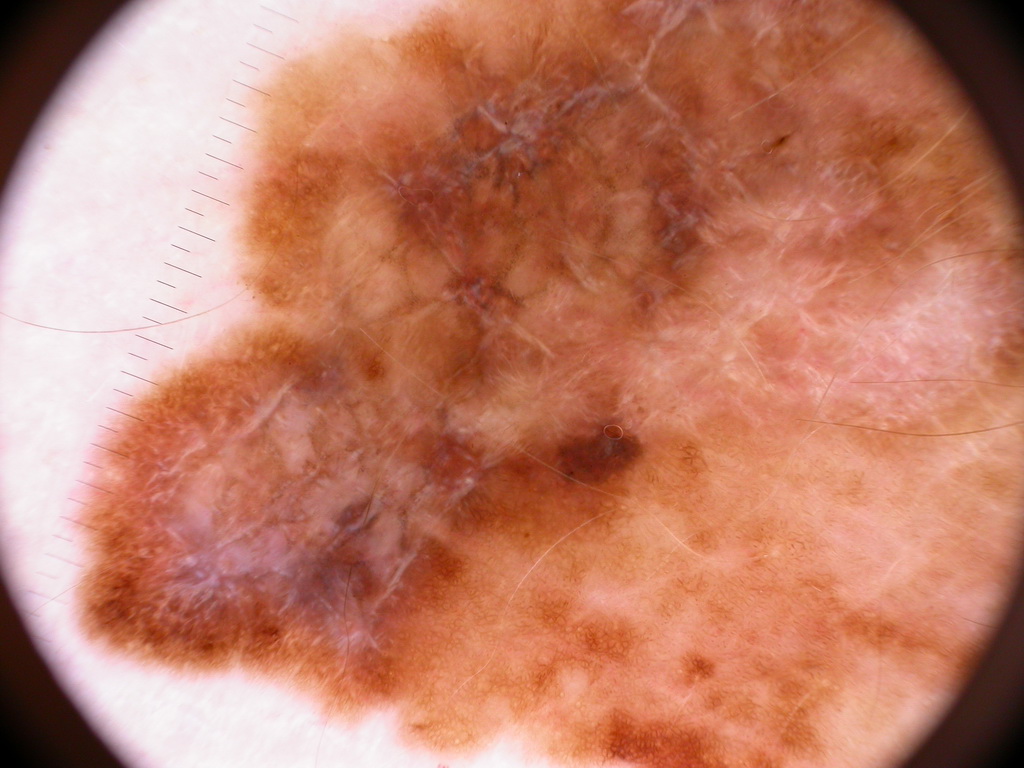modality = dermoscopy | subject = male, aged 68 to 72 | field coverage = spans the dermoscopic field | dermoscopic pattern = pigment network and negative network; absent: globules, milia-like cysts, and streaks | diagnosis = a melanoma, a malignancy.